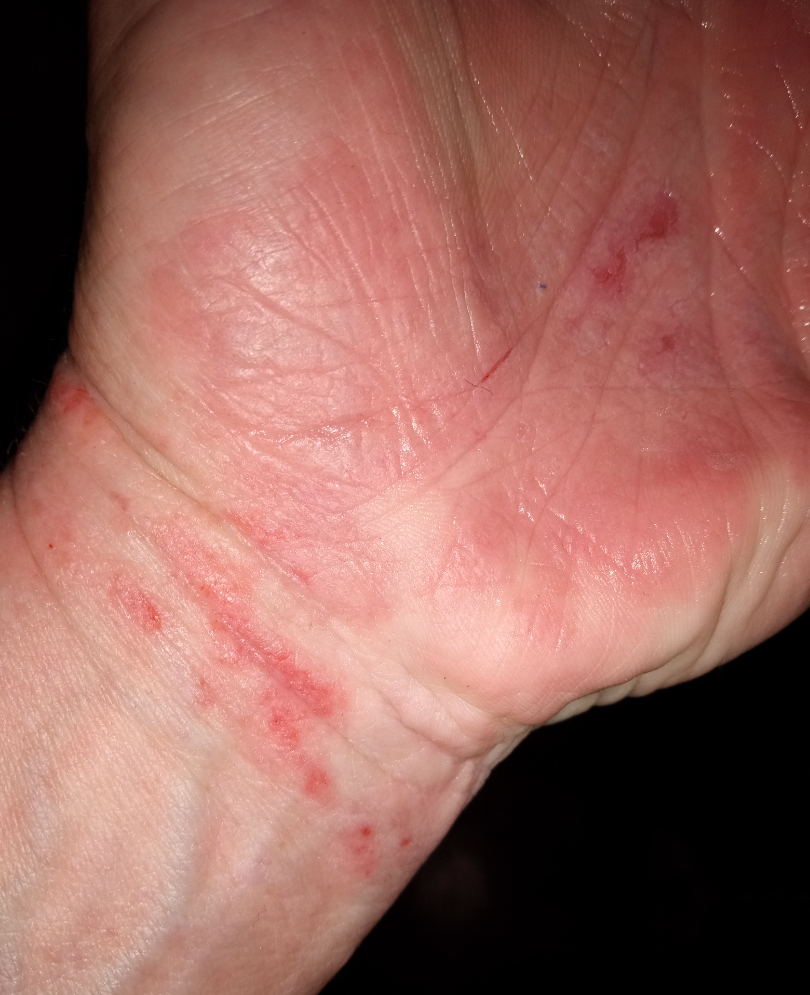One reviewing dermatologist: Allergic Contact Dermatitis and Irritant Contact Dermatitis were each considered, in no particular order.